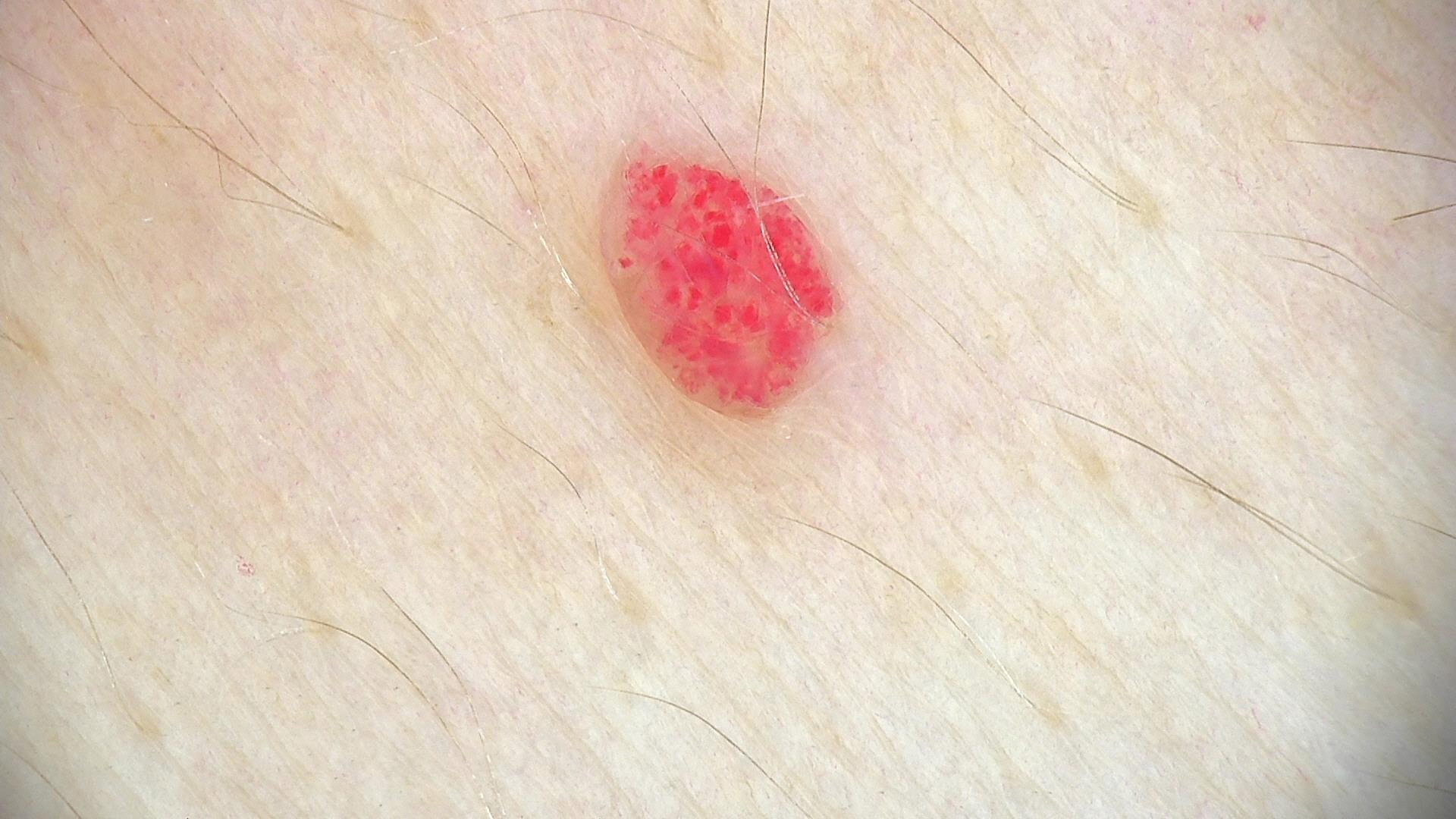  image: dermoscopy
  diagnosis:
    name: hemangioma
    code: ha
    malignancy: benign
    super_class: non-melanocytic
    confirmation: expert consensus